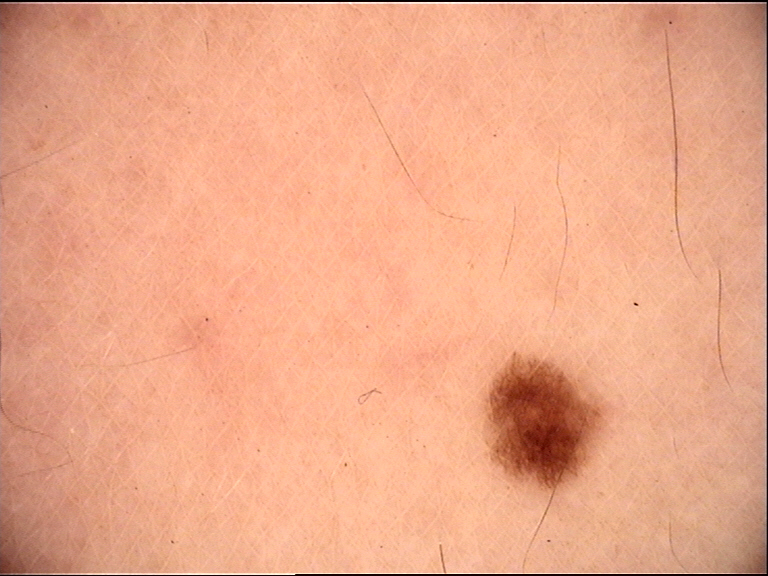modality = dermoscopy, category = banal, assessment = junctional nevus (expert consensus).